The arm is involved. The patient is 30–39, female. The photograph is a close-up of the affected area — 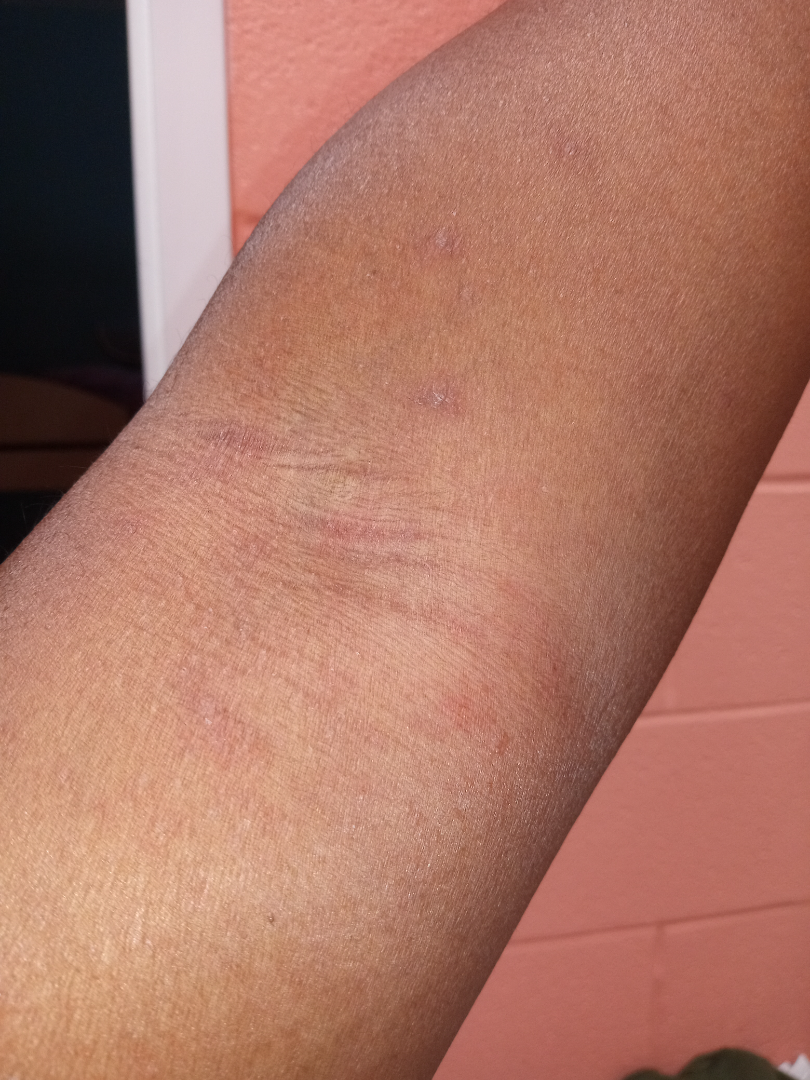{"differential": "Eczema"}